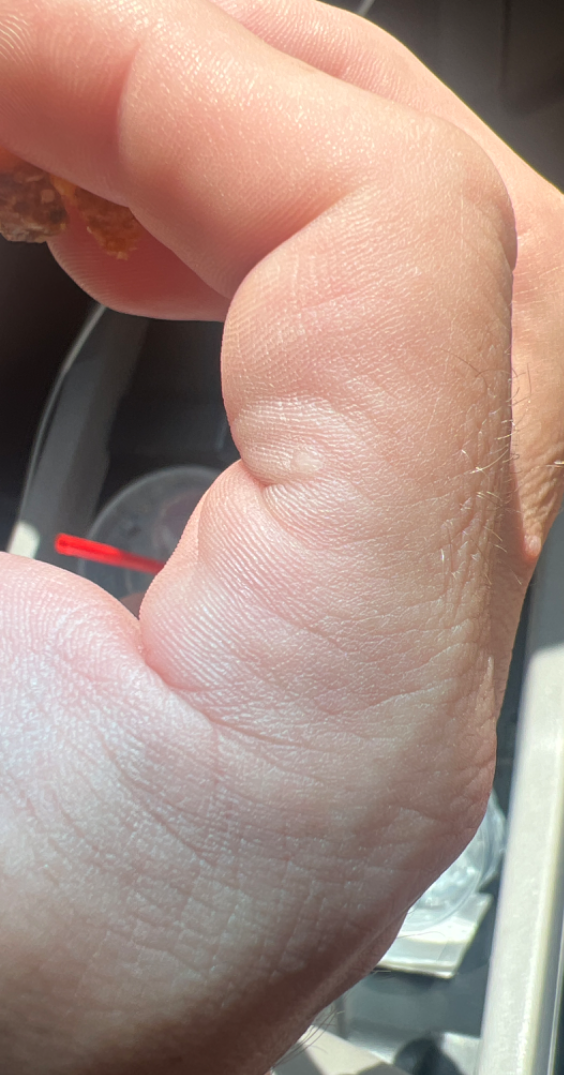The skin condition could not be confidently assessed from this image.